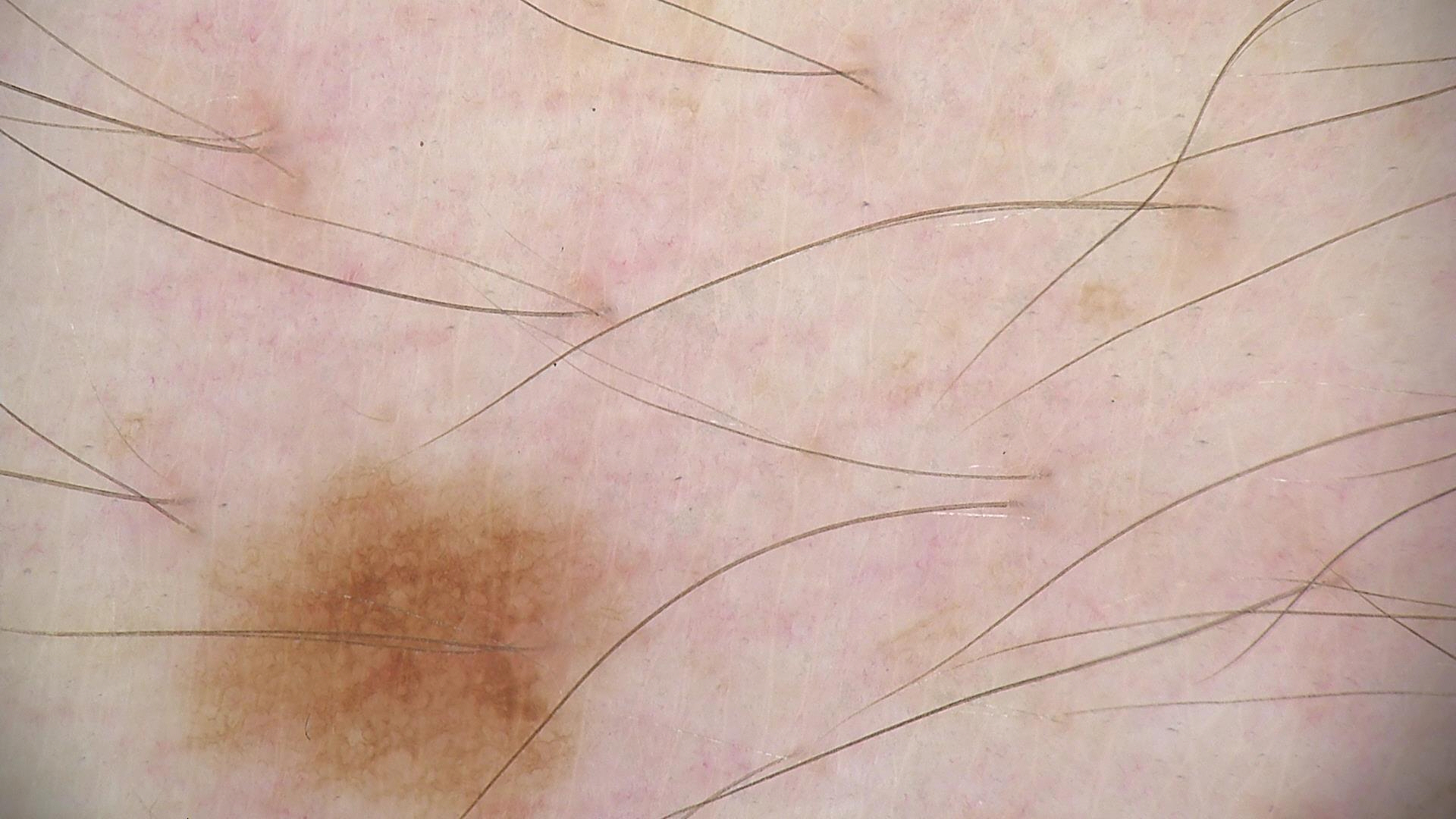{"image": "dermoscopy", "diagnosis": {"name": "dysplastic junctional nevus", "code": "jd", "malignancy": "benign", "super_class": "melanocytic", "confirmation": "expert consensus"}}